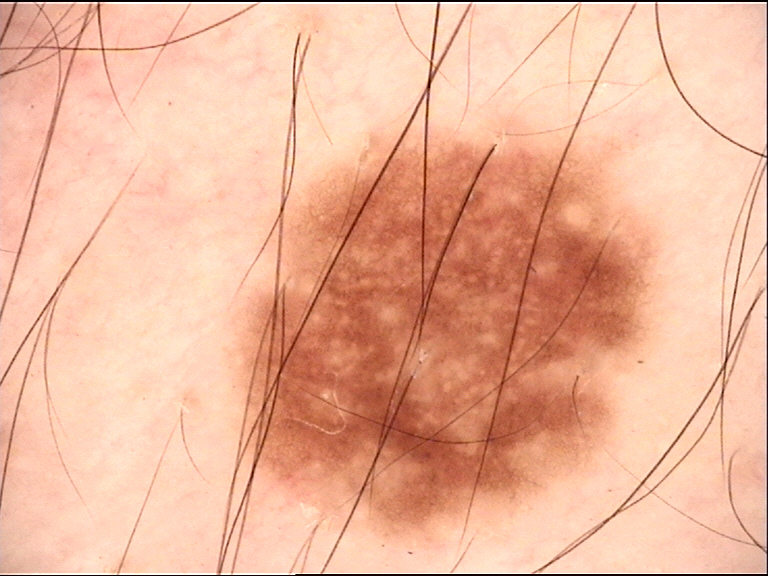Diagnosed as a dysplastic junctional nevus.